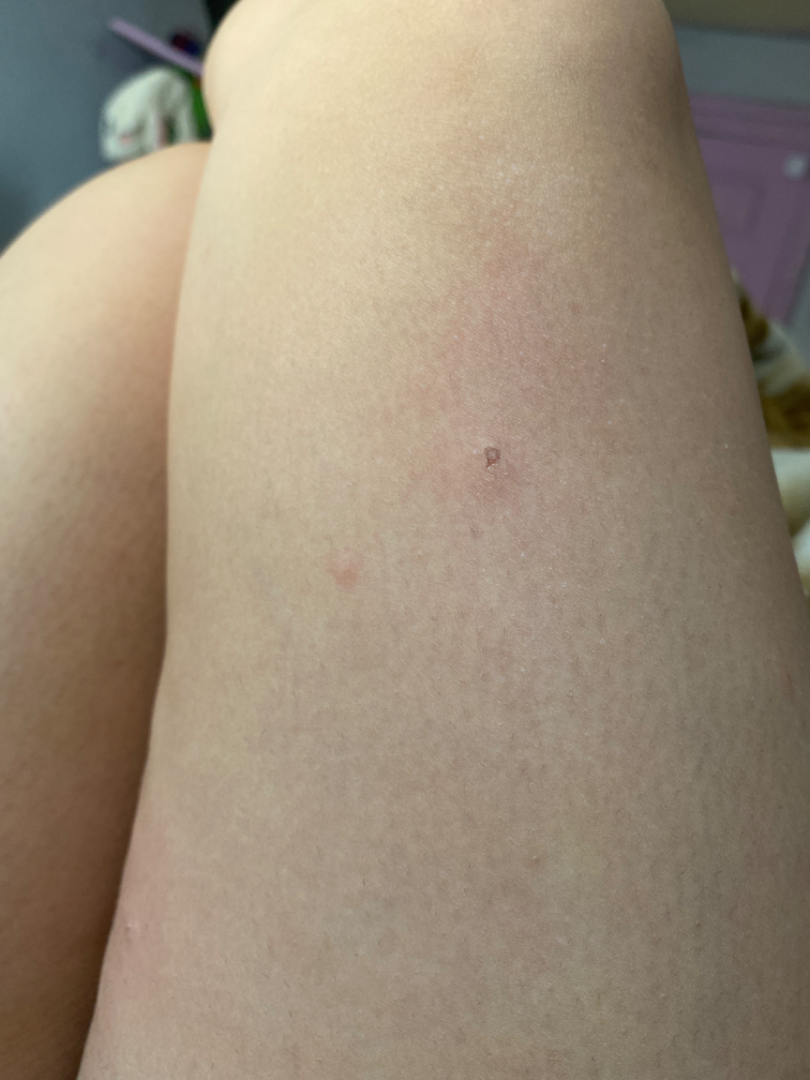| key | value |
|---|---|
| assessment | indeterminate |
| skin tone | Fitzpatrick phototype IV |
| view | at a distance |